The lesion involves the arm; the patient is 18–29, female; a close-up photograph: 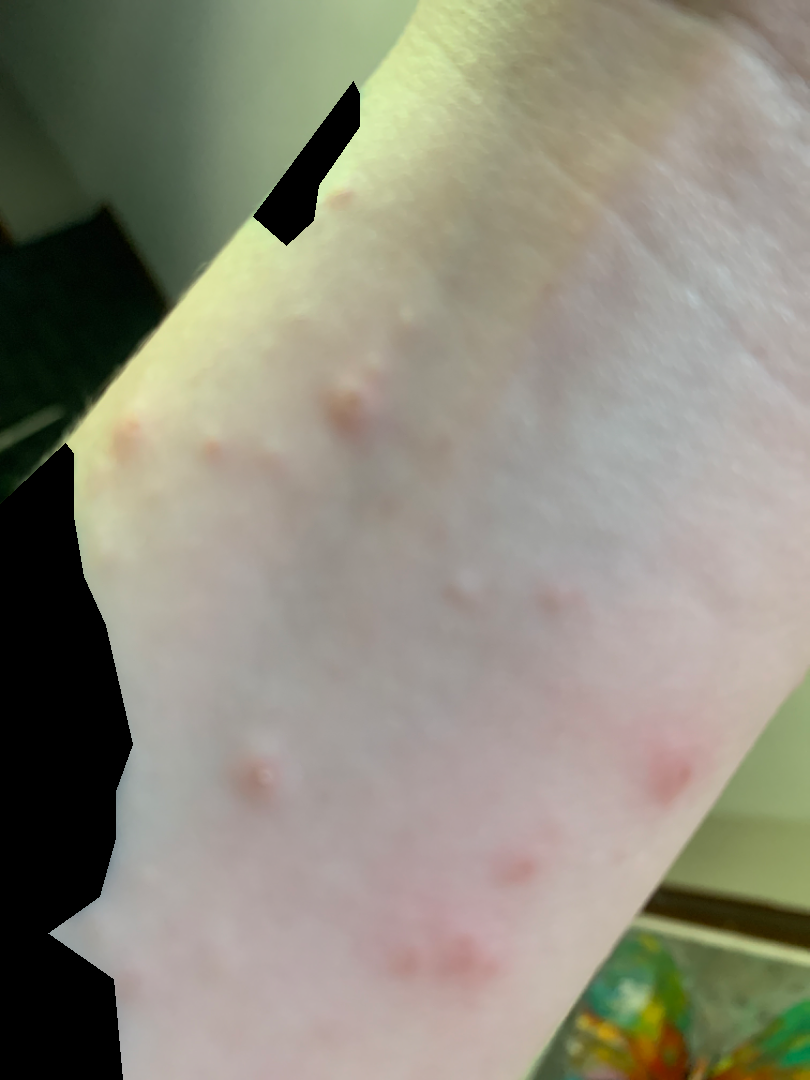self-categorized as=a rash | skin tone=FST II | texture=raised or bumpy | duration=less than one week | lesion symptoms=itching | dermatologist impression=Scabies and Insect Bite were each considered, in no particular order.